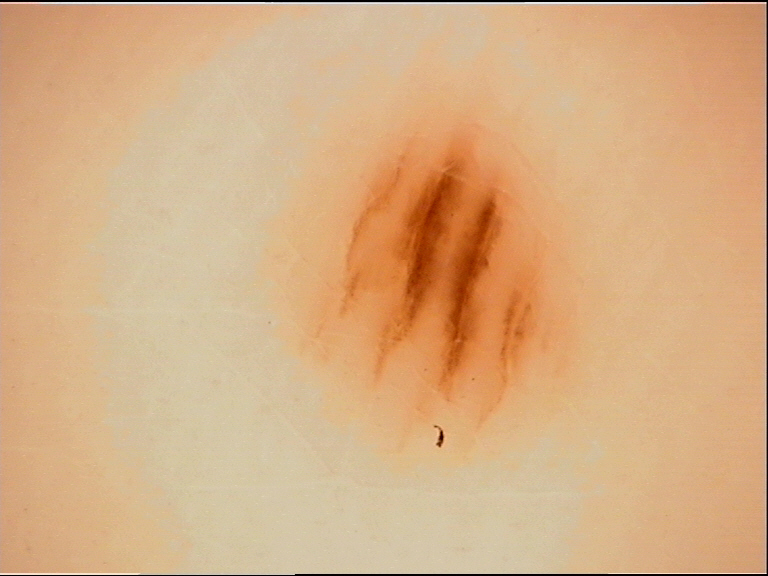Classified as an acral junctional nevus.